A dermoscopic close-up of a skin lesion.
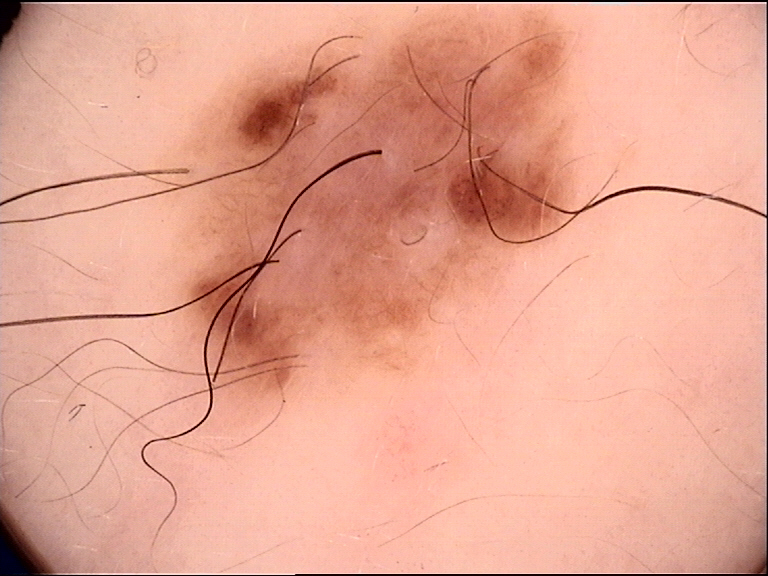diagnosis: dysplastic compound nevus (expert consensus).